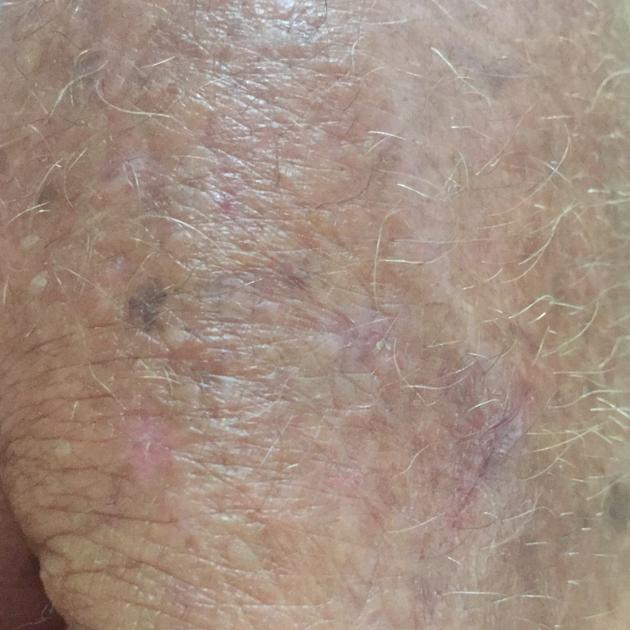A clinical photo of a skin lesion taken with a smartphone.
The lesion involves a hand.
By the patient's account, the lesion does not itch and is not elevated.
The consensus clinical diagnosis was a premalignant lesion — an actinic keratosis.